A dermoscopic image of a skin lesion:
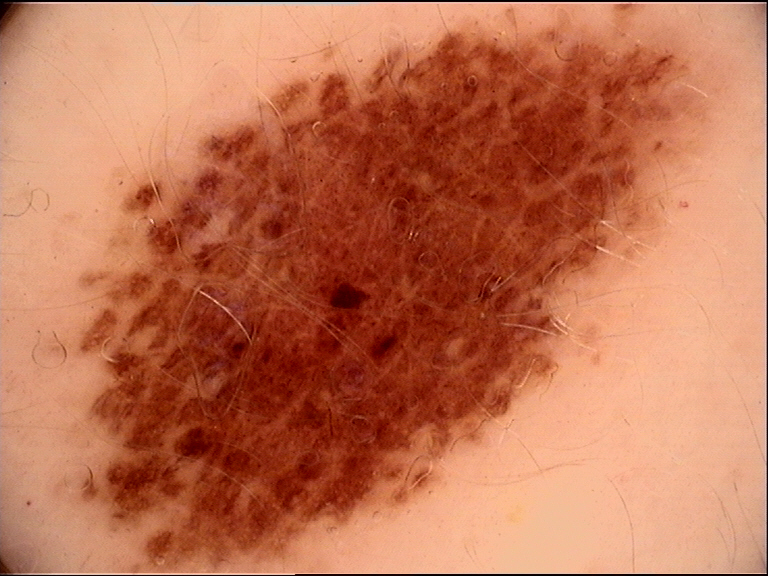Conclusion: Labeled as a benign lesion — a dysplastic junctional nevus.